A male subject about 20 years old. A dermoscopy image of a single skin lesion: 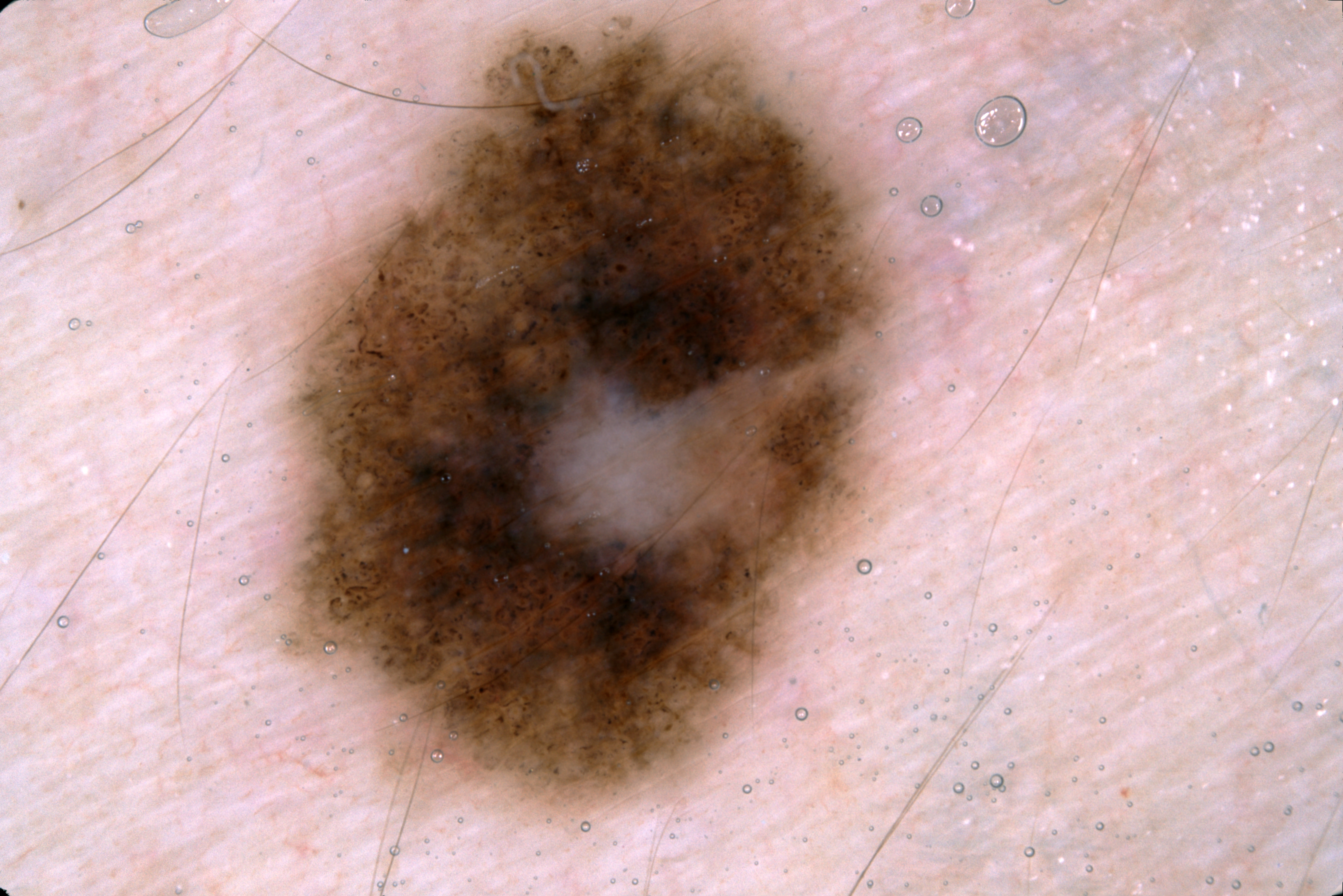Dermoscopic review identifies milia-like cysts, pigment network, and negative network; no streaks. The lesion is bounded by [284, 21, 902, 812]. The lesion takes up about 30% of the image. Clinically diagnosed as a melanocytic nevus, a benign lesion.